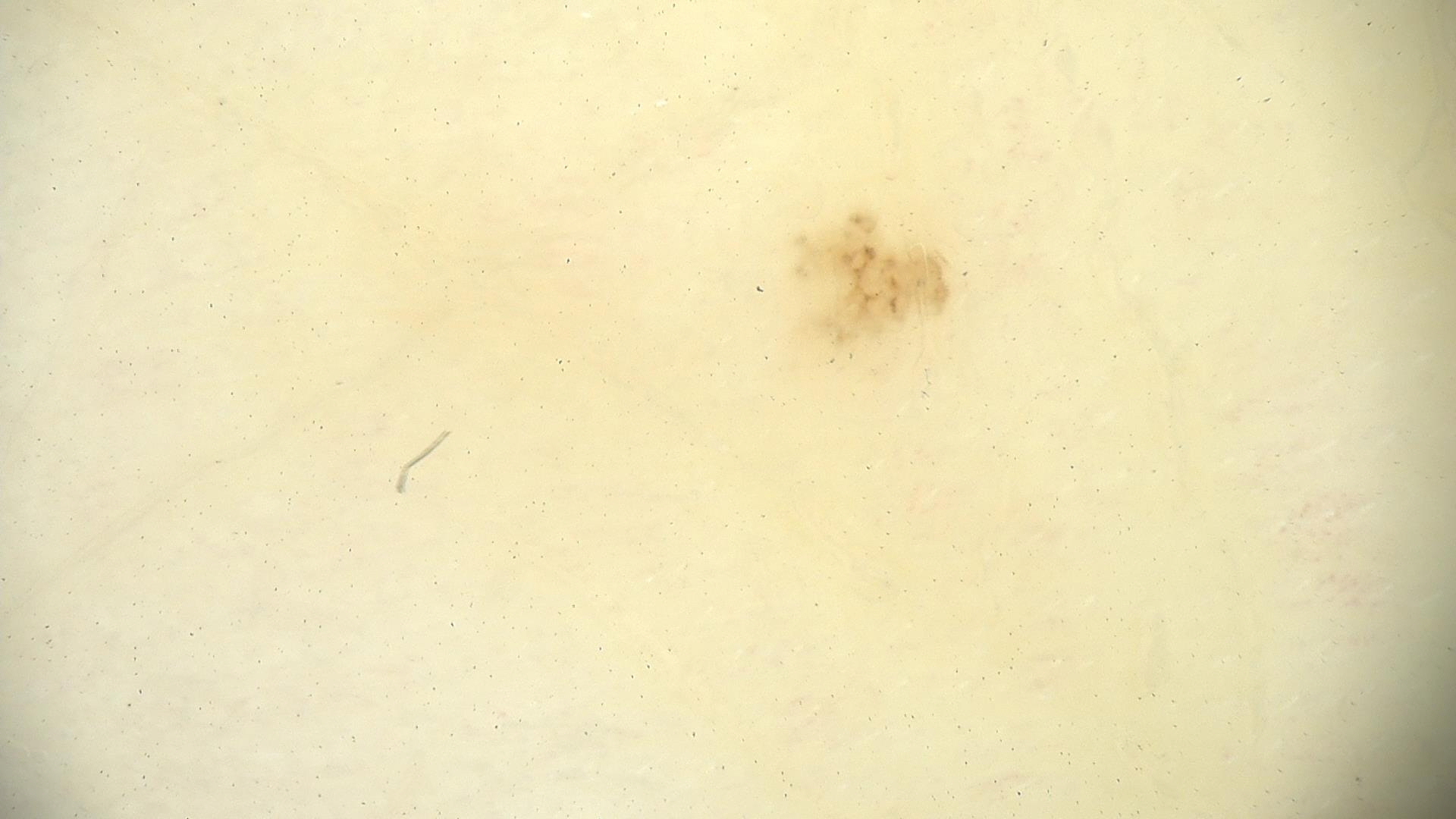label — acral dysplastic junctional nevus (expert consensus).